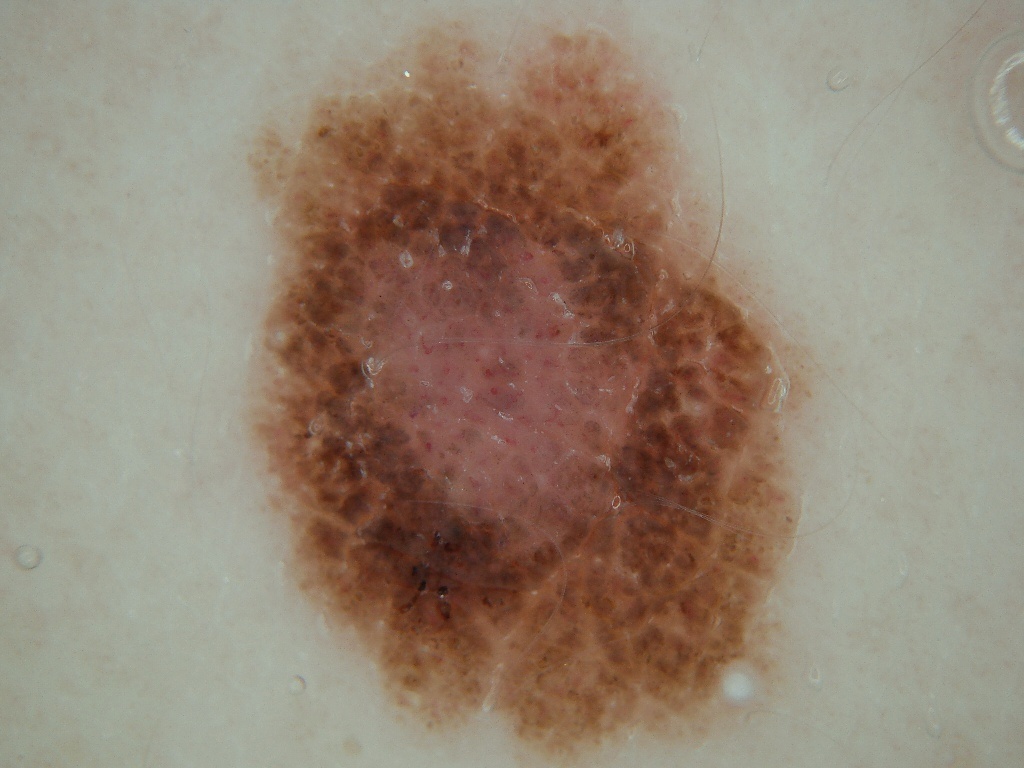A dermoscopy image of a single skin lesion. The lesion takes up a large portion of the image. As (left, top, right, bottom), the lesion's extent is 234 15 836 766. Diagnosed as a benign skin lesion.